The leg is involved. Texture is reported as rough or flaky. The lesion is associated with bothersome appearance, itching and enlargement. Present for one to three months. This is a close-up image. Self-categorized by the patient as a rash.
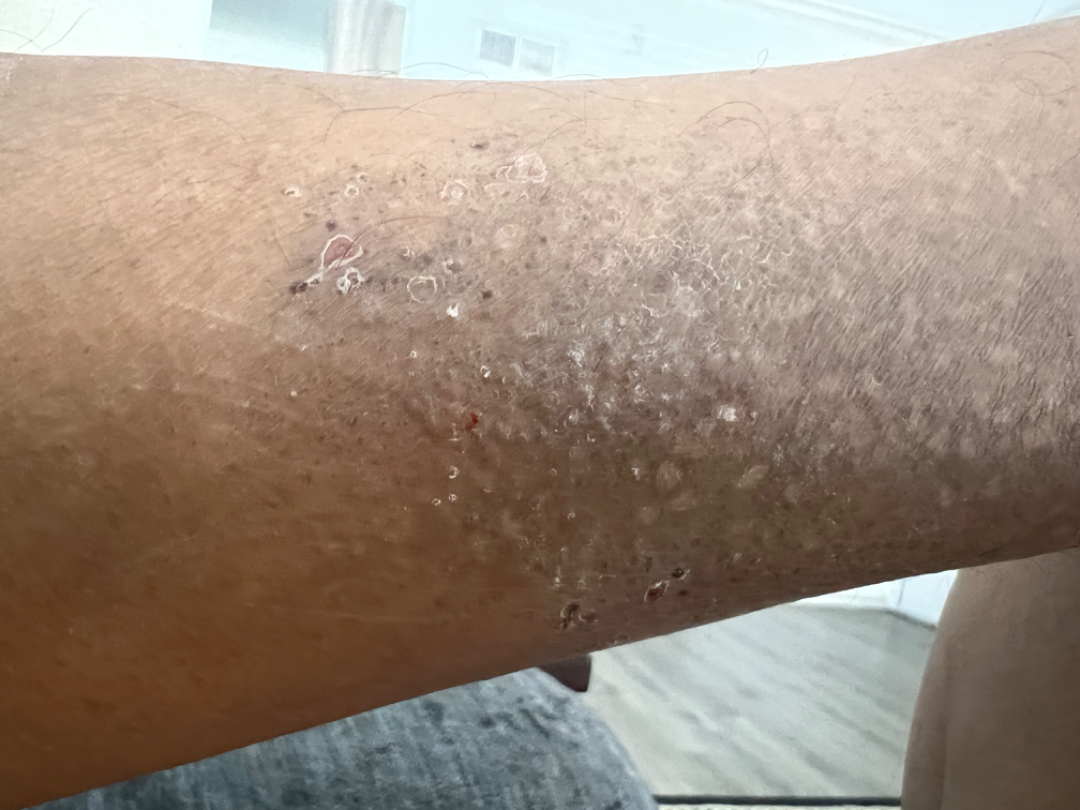The leading consideration is Lichen Simplex Chronicus; an alternative is Eczema.